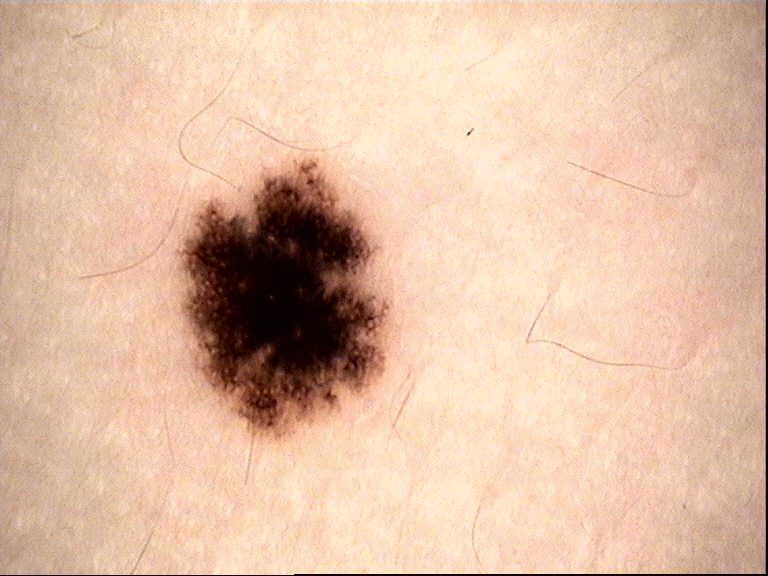| feature | finding |
|---|---|
| imaging | dermatoscopy |
| assessment | dysplastic junctional nevus (expert consensus) |